A dermoscopic photograph of a skin lesion: 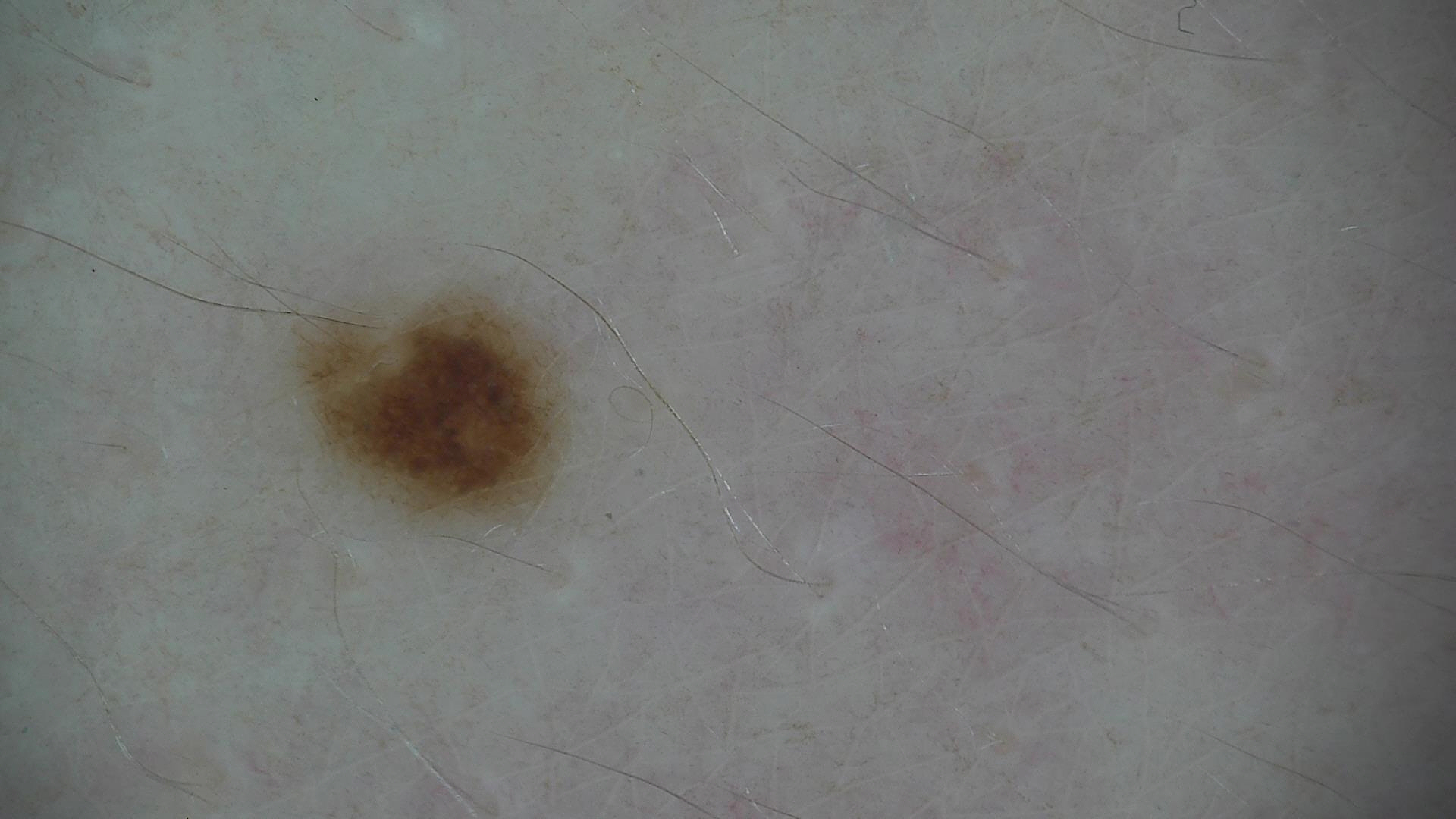The diagnosis was a benign lesion — a dysplastic junctional nevus.